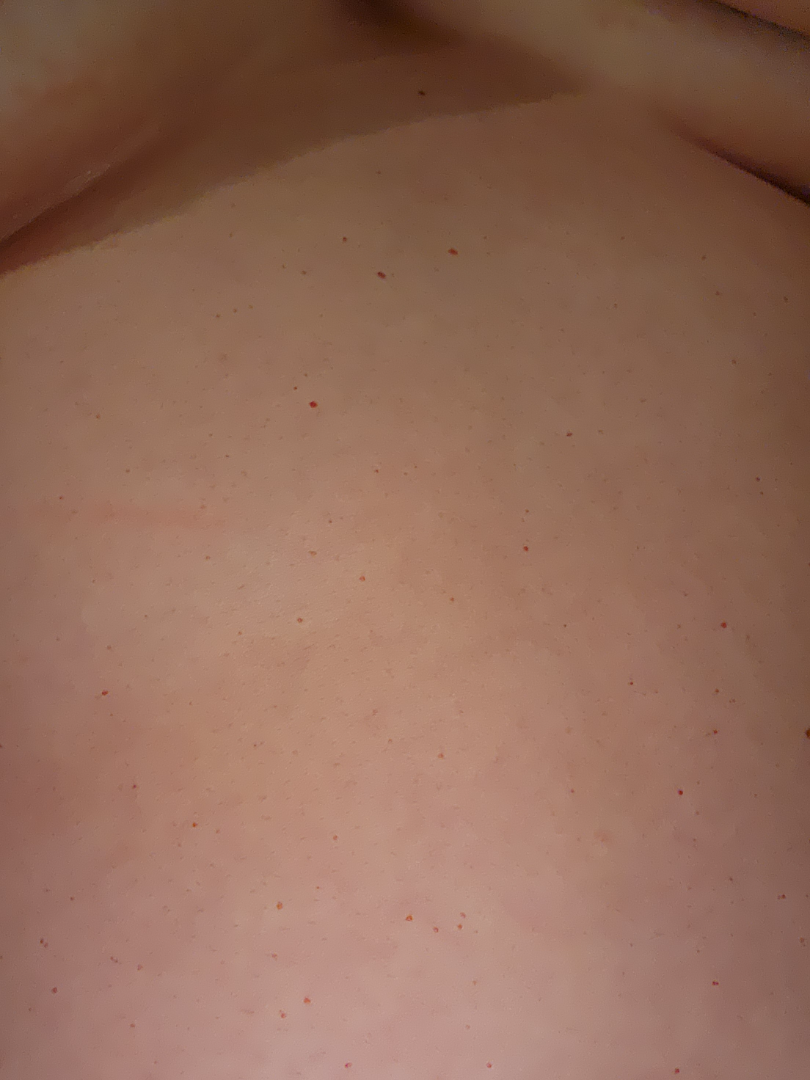present for = more than five years; patient's own categorization = a pigmentary problem; subject = female; constitutional symptoms = fatigue; body site = front of the torso and back of the torso; texture = flat; reported symptoms = bothersome appearance; shot type = at an angle; diagnostic considerations = in keeping with Hemangioma.